A male subject roughly 40 years of age; a contact-polarized dermoscopy image of a skin lesion — 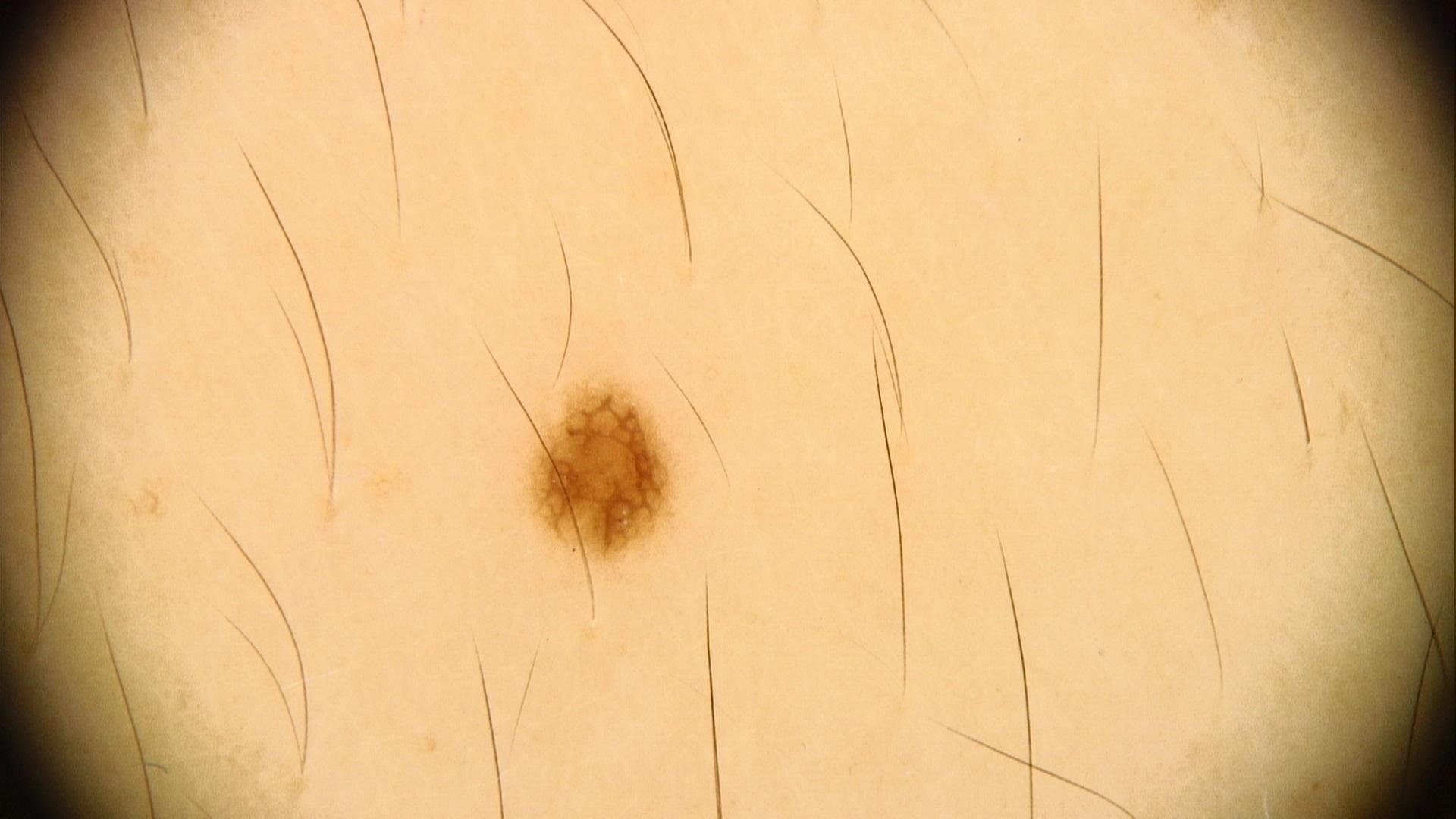diagnostic label: Nevus (clinical impression).